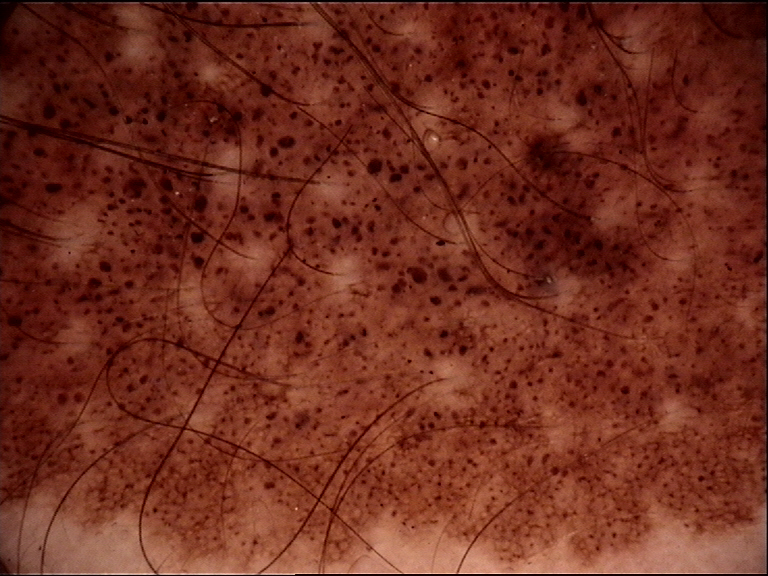assessment — congenital compound nevus (expert consensus).